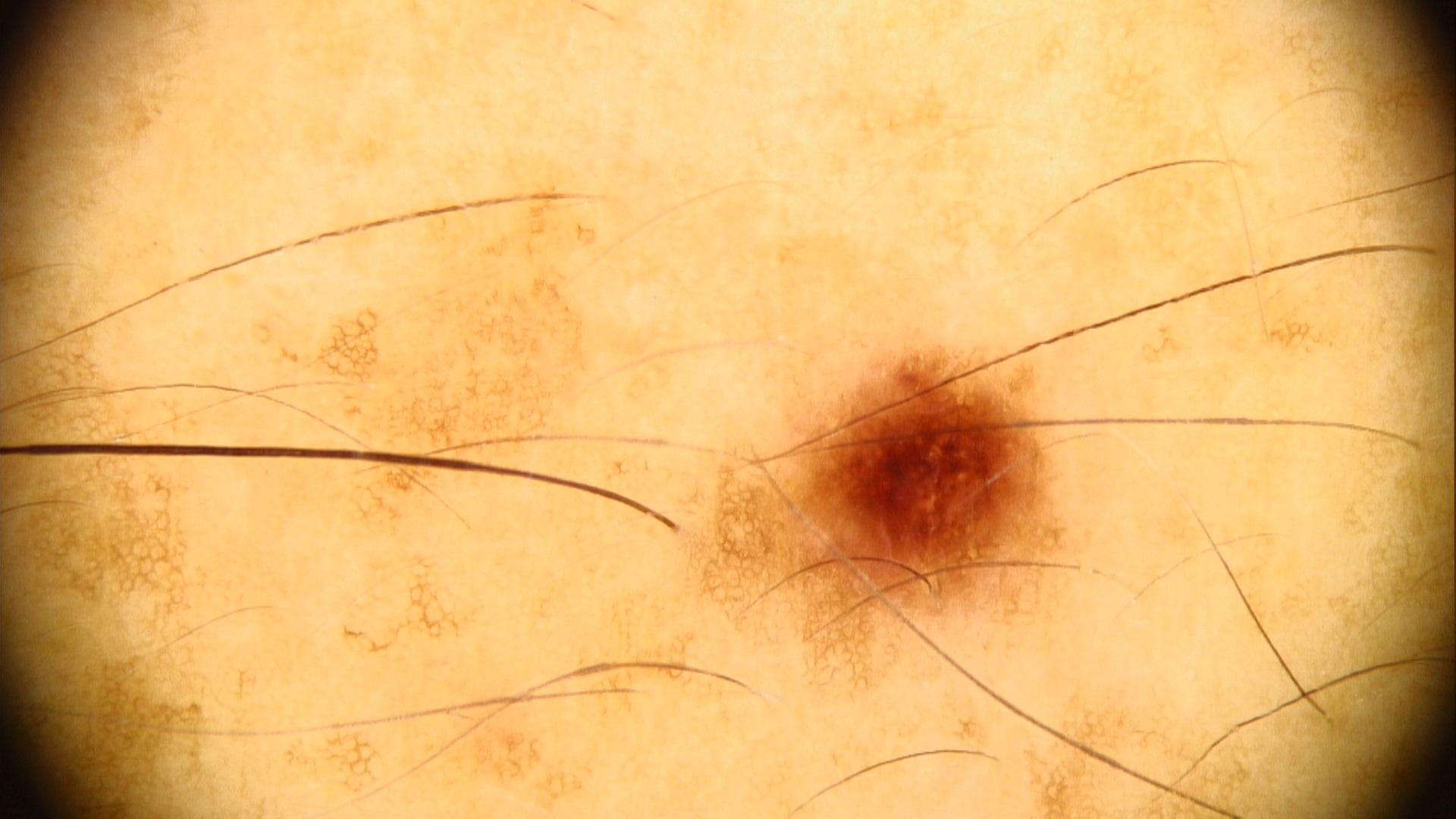Notes:
- relevant background · no first-degree relative with melanoma and no prior melanoma
- subject · male, about 40 years old
- skin type · III
- image type · contact-polarized dermoscopy
- body site · the posterior trunk
- impression · Nevus